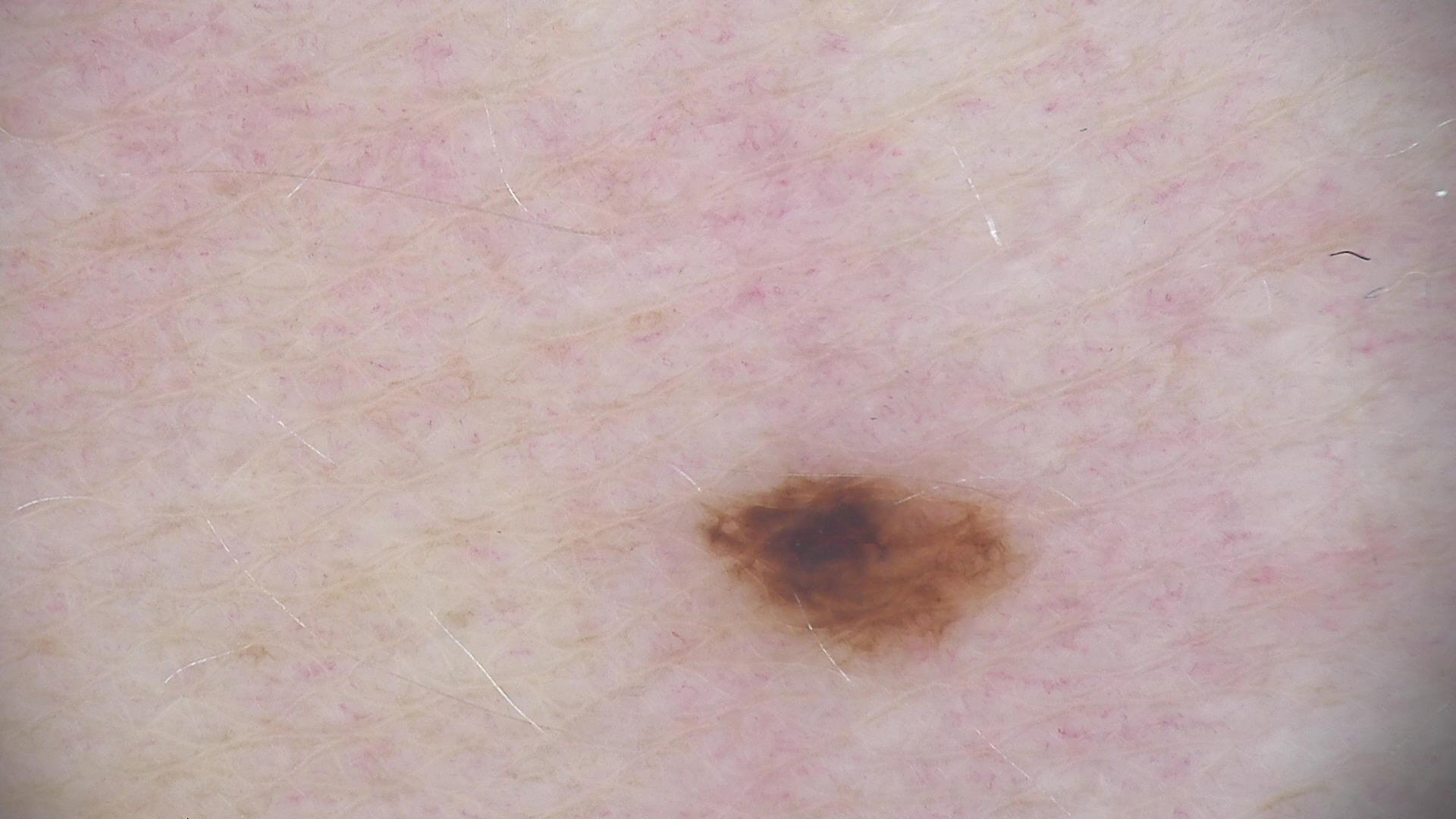Classified as a dysplastic junctional nevus.